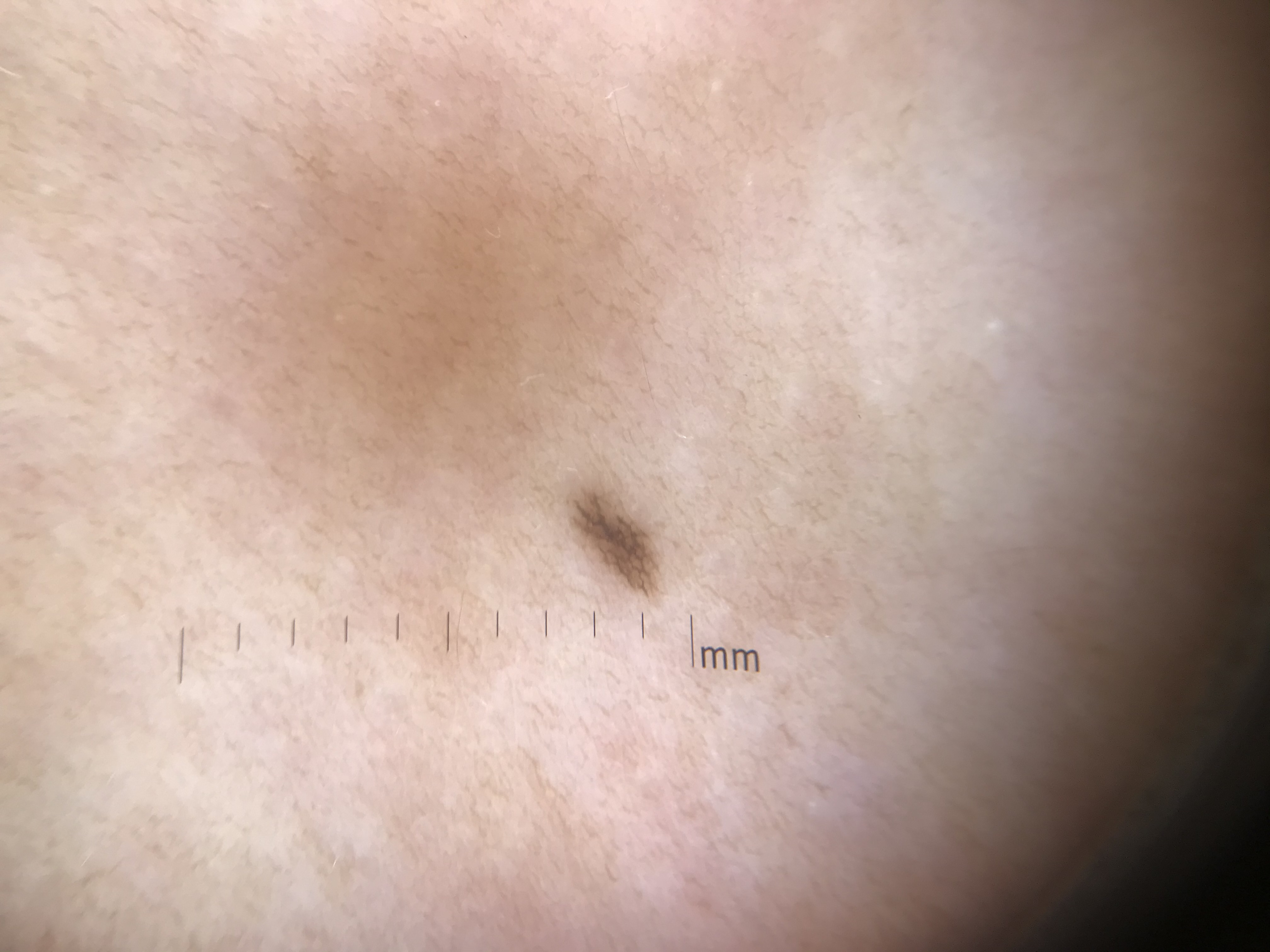diagnostic label = junctional nevus (expert consensus).